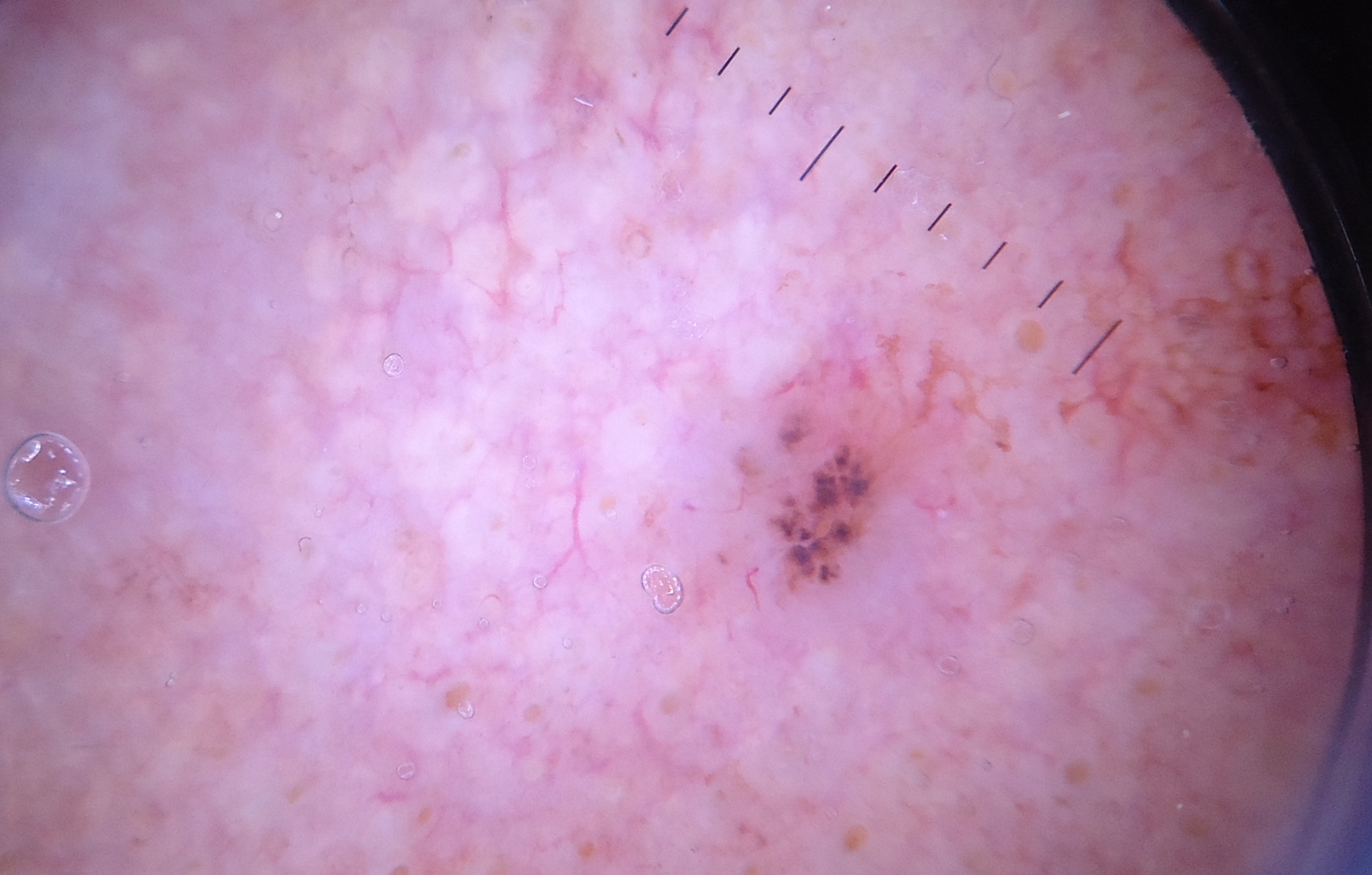Conclusion: The biopsy diagnosis was a basal cell carcinoma.